Texture is reported as rough or flaky · the photograph was taken at an angle · the lesion involves the palm, arm and back of the hand · self-categorized by the patient as acne · FST V; non-clinician graders estimated Monk Skin Tone 7 (US pool) or 5 (India pool) · female patient, age 60–69 · the patient also reports fatigue · the contributor reports the condition has been present for three to twelve months: 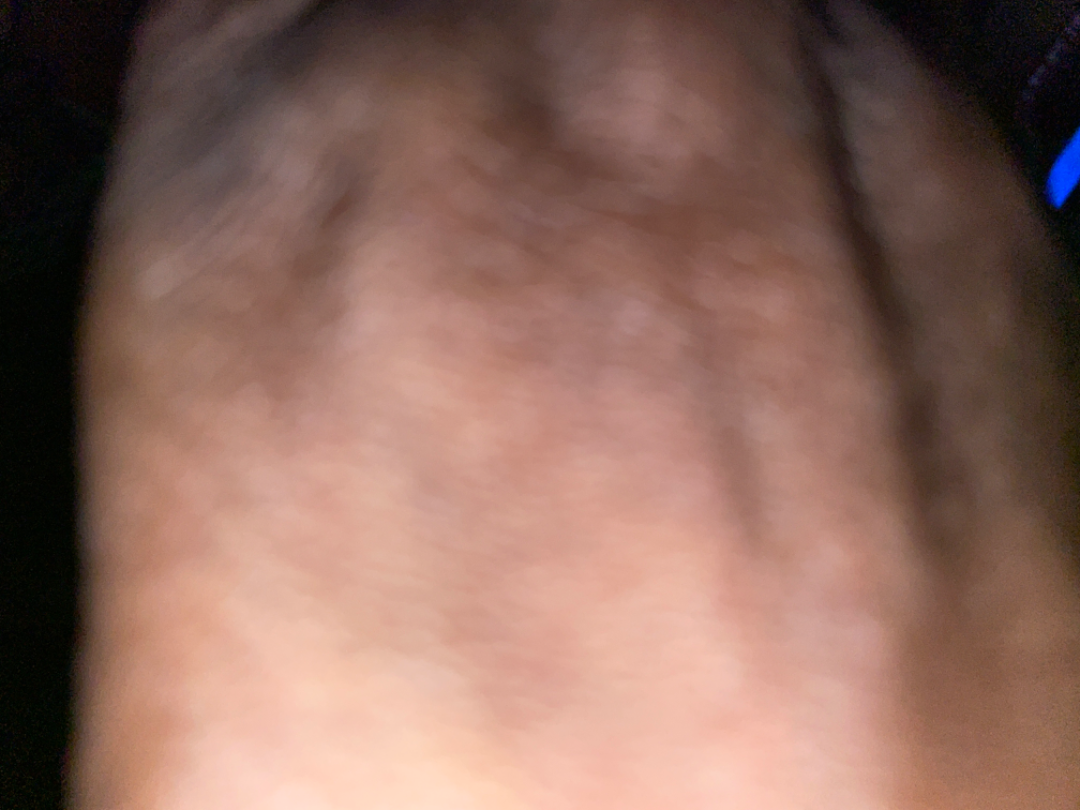The reviewer was unable to grade this case for skin condition.